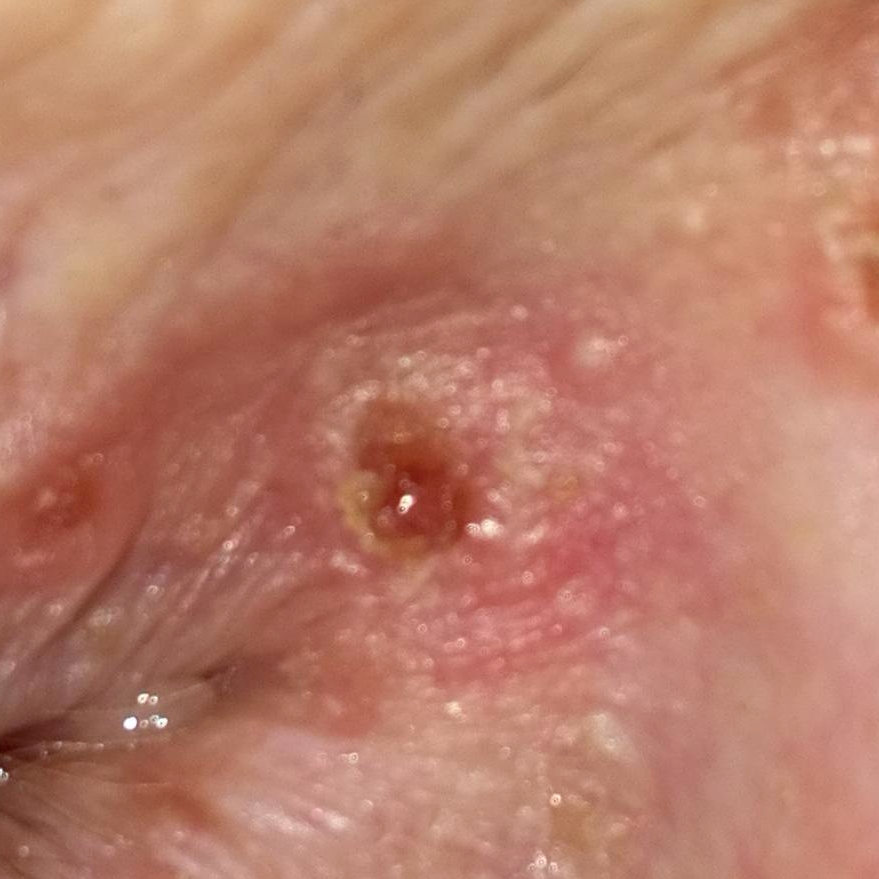A female subject 62 years old. A smartphone photograph of a skin lesion. Skin type II. The lesion was found on the face. Per patient report, the lesion has bled, has grown, is elevated, and itches. Confirmed on histopathology as a basal cell carcinoma.